Female contributor, age 18–29; no associated systemic symptoms reported; the photograph is a close-up of the affected area; the contributor notes itching; texture is reported as raised or bumpy; the leg is involved; the patient described the issue as a rash:
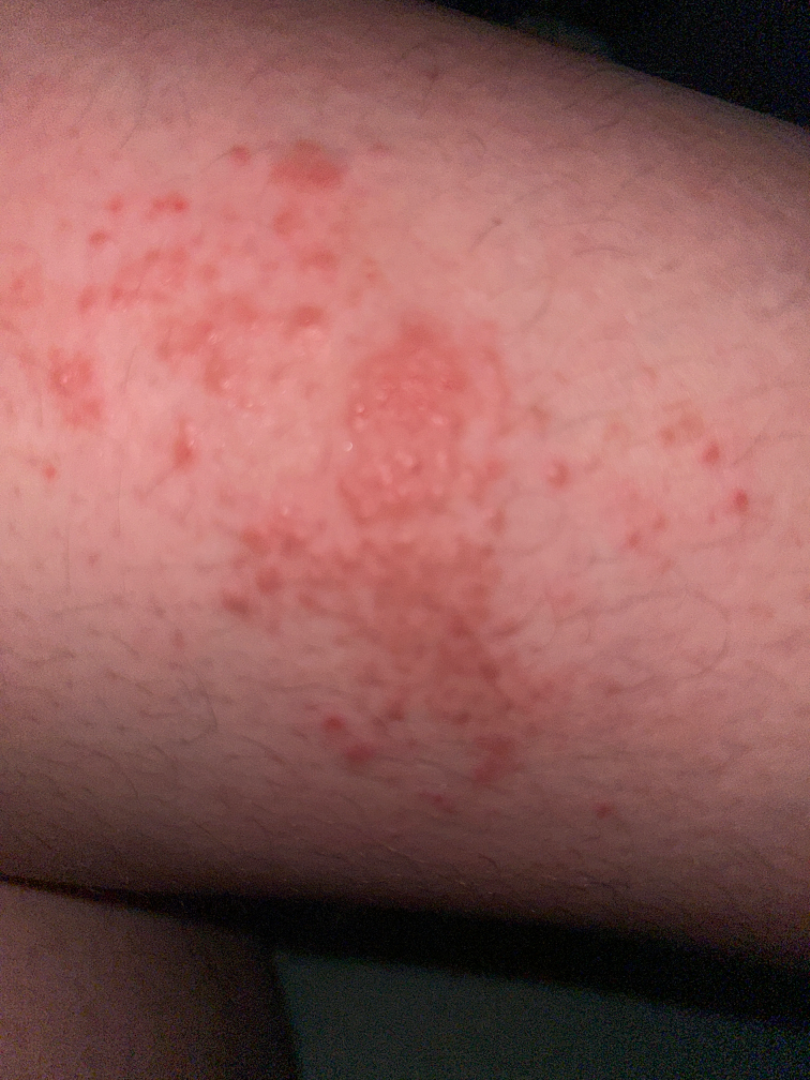impression: most consistent with Allergic Contact Dermatitis.